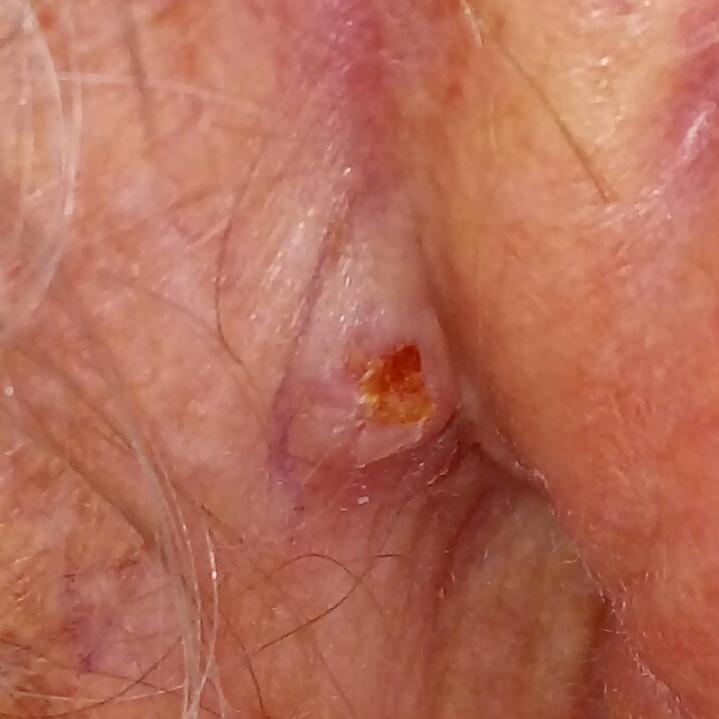Summary:
A male subject 71 years of age. A clinical close-up photograph of a skin lesion. History notes no pesticide exposure. The lesion was found on an ear. The lesion is roughly 10 by 6 mm.
Conclusion:
On biopsy, the diagnosis was a malignant lesion — a basal cell carcinoma.